A dermoscopic close-up of a skin lesion: 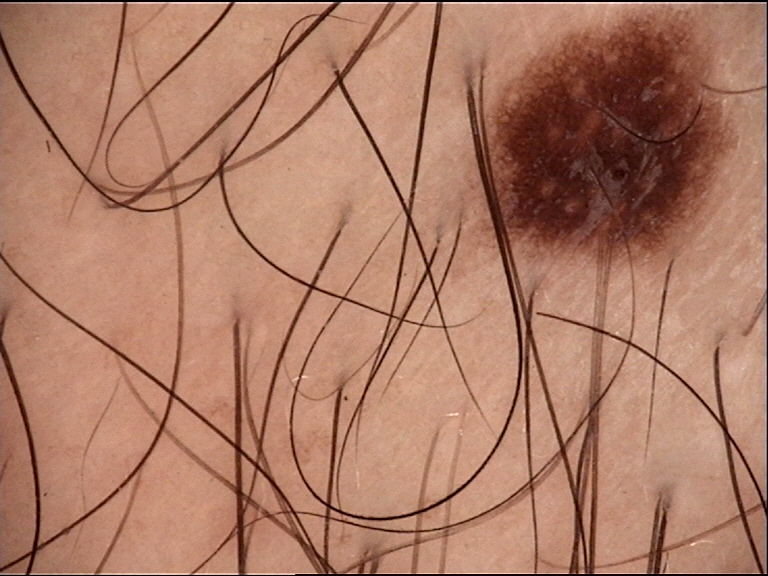Findings:
* lesion type · banal
* diagnosis · junctional nevus (expert consensus)